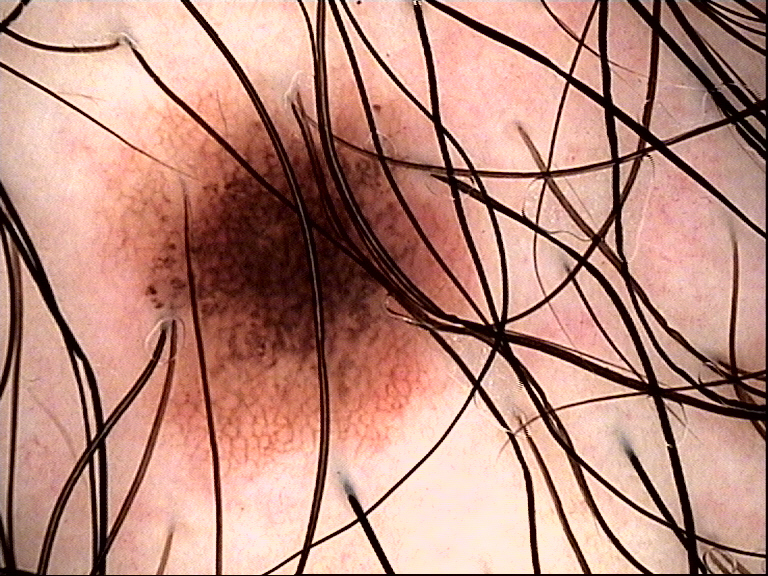{"image": "dermoscopy", "diagnosis": {"name": "dysplastic compound nevus", "code": "cd", "malignancy": "benign", "super_class": "melanocytic", "confirmation": "expert consensus"}}